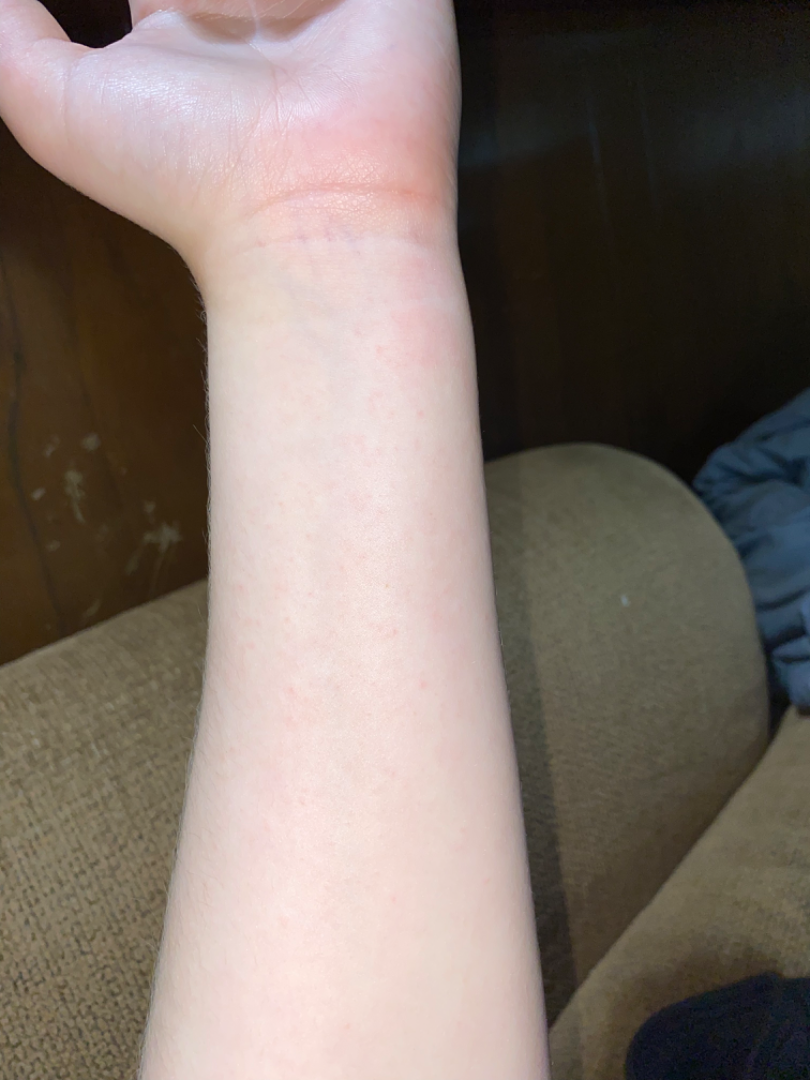The skin findings could not be characterized from the image. The patient reported no systemic symptoms. The photograph was taken at a distance. The arm is involved. The lesion is associated with itching. The patient is a female aged 18–29. Self-categorized by the patient as a rash. Reported duration is about one day. Fitzpatrick phototype I.